No associated lesion symptoms were reported. The patient described the issue as a rash. Reported duration is about one day. A close-up photograph. Male contributor, age 18–29. Located on the back of the torso:
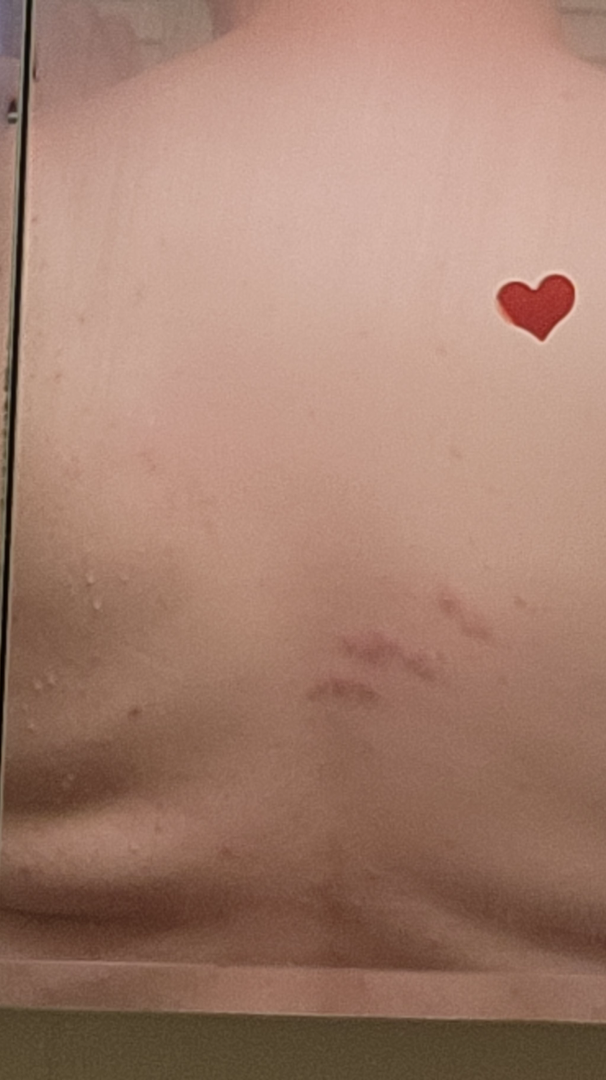No differential diagnosis could be assigned on photographic review.